The top or side of the foot, leg, back of the torso and arm are involved. Female contributor, age 50–59. The photograph is a close-up of the affected area:
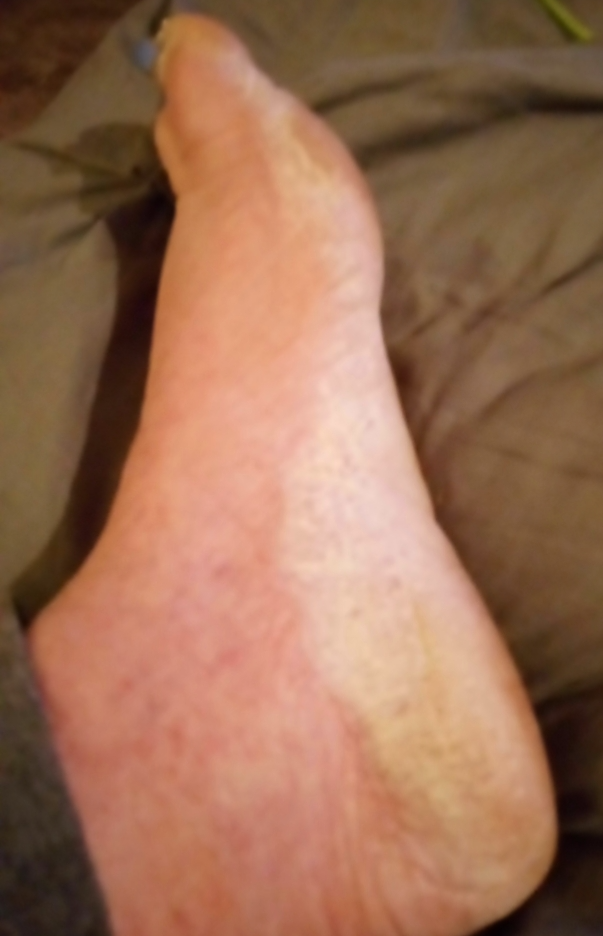{"symptoms": ["bothersome appearance", "itching", "burning", "enlargement"], "skin_tone": {"fitzpatrick": "III", "monk_skin_tone": [2, 3]}, "texture": "raised or bumpy", "duration": "one to three months", "differential": {"leading": ["Keratoderma"], "considered": ["Hyperkeratosis"]}}